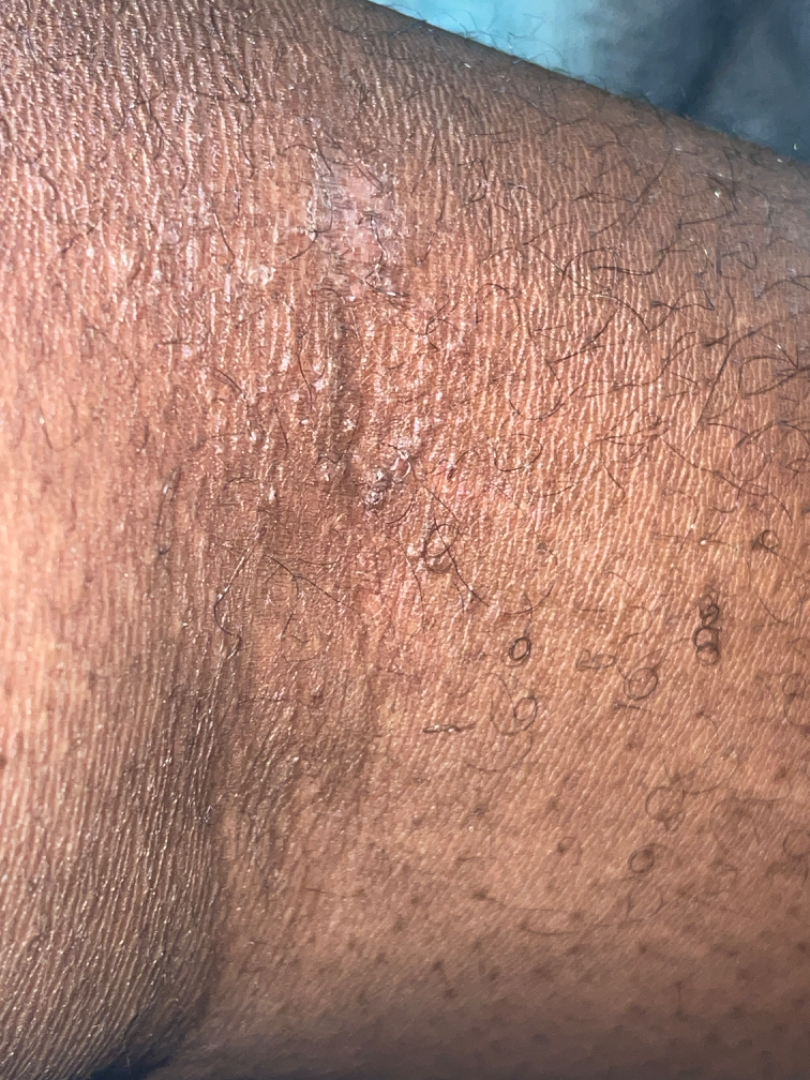Review:
On photographic review by a dermatologist: in keeping with Eczema.